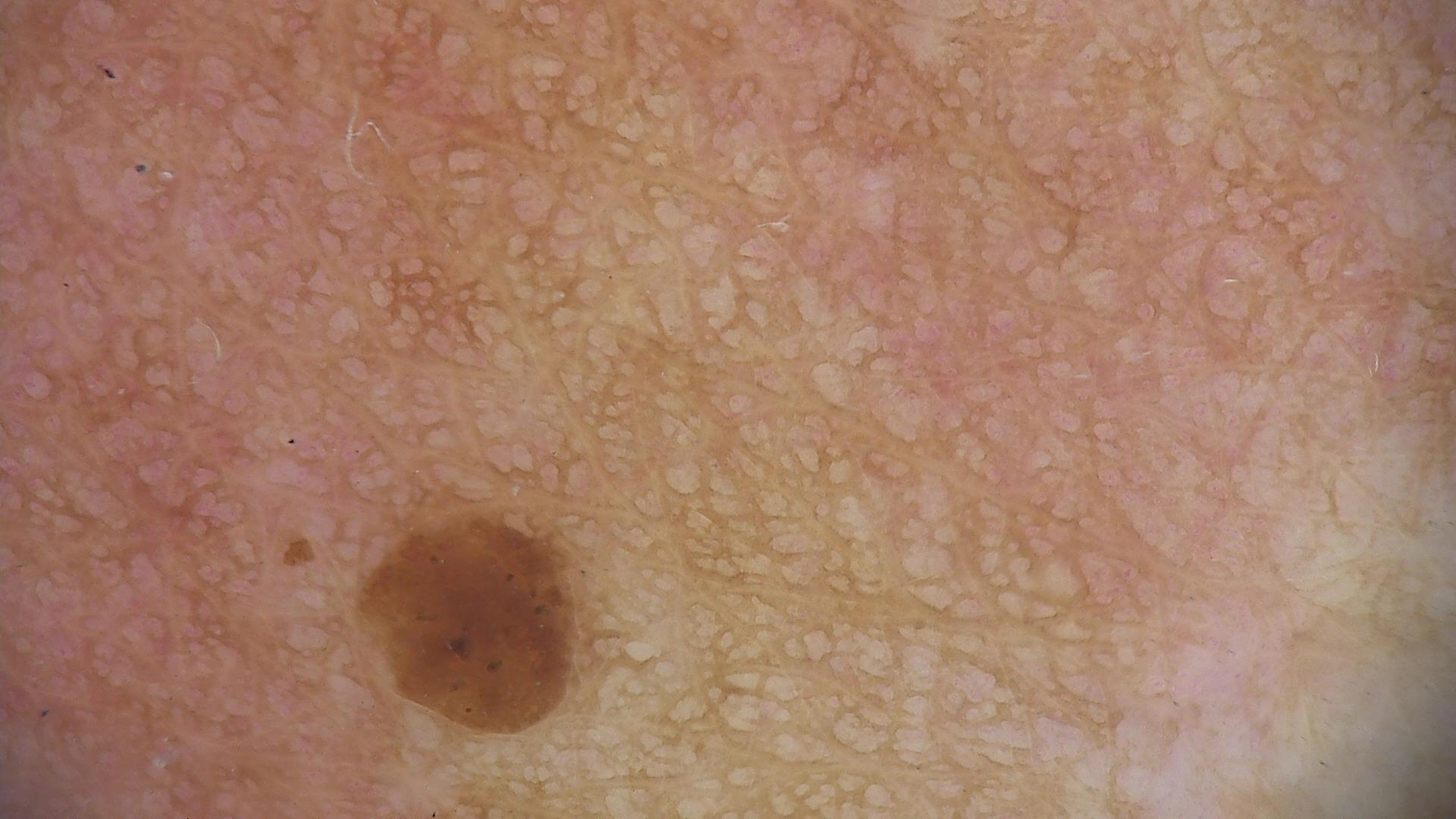| feature | finding |
|---|---|
| image | dermoscopy |
| assessment | seborrheic keratosis (expert consensus) |